The photo was captured at an angle; the top or side of the foot and sole of the foot are involved; the lesion is described as rough or flaky; present for one to three months; the contributor is 18–29, female; reported lesion symptoms include bothersome appearance, itching and bleeding; FST II.
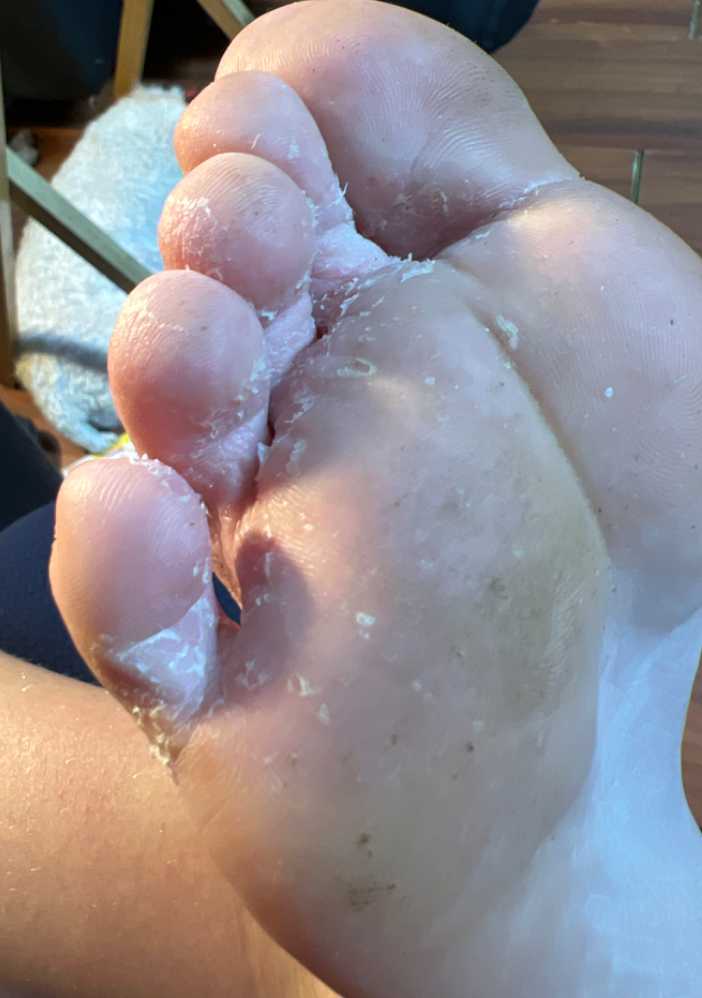On remote review of the image, most likely Tinea; less likely is Eczema; less probable is Allergic Contact Dermatitis.